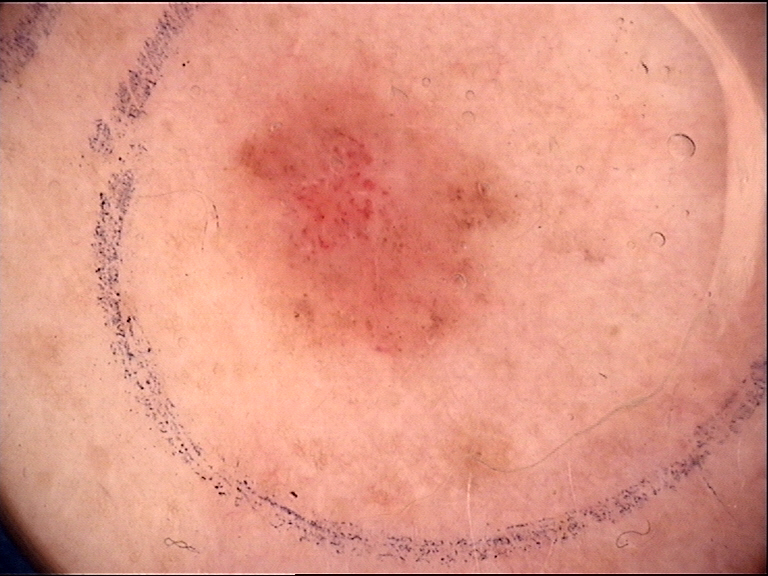Summary: A dermoscopic image of a skin lesion. Impression: Labeled as a benign lesion — a dysplastic junctional nevus.